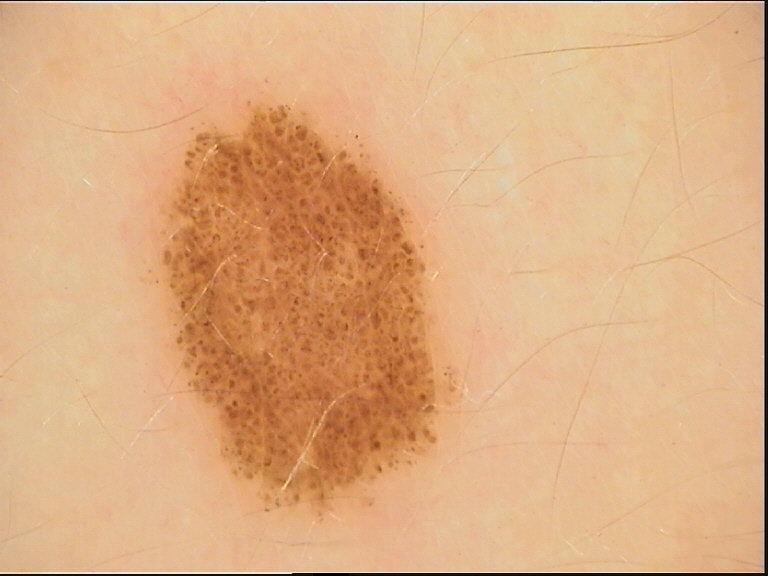Summary: A dermatoscopic image of a skin lesion. Conclusion: The diagnostic label was a benign lesion — a dysplastic junctional nevus.